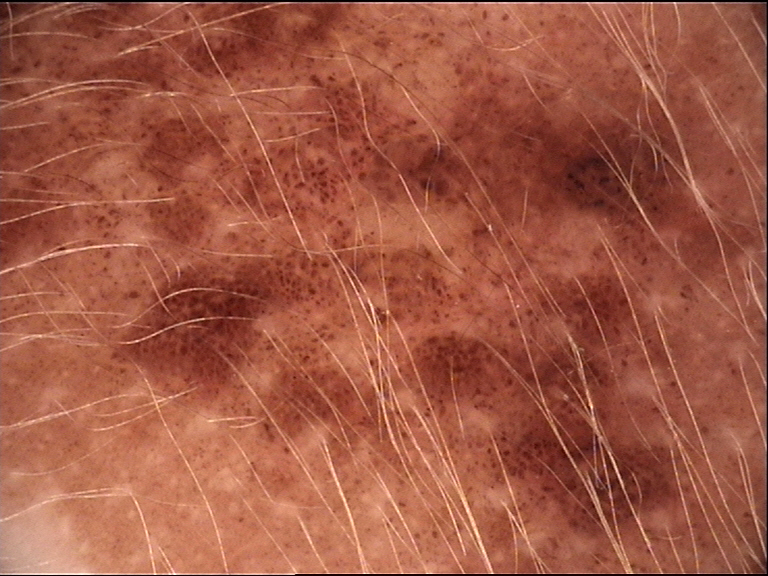Conclusion:
The diagnosis was a banal lesion — a congenital junctional nevus.